The patient considered this a growth or mole. The lesion is described as rough or flaky and raised or bumpy. The back of the hand is involved. Fitzpatrick I; lay reviewers estimated Monk Skin Tone 2 (US pool) or 1 (India pool). Female subject, age 30–39. The lesion is associated with pain, enlargement and bothersome appearance. Associated systemic symptoms include joint pain. The condition has been present for more than one year. This image was taken at an angle: 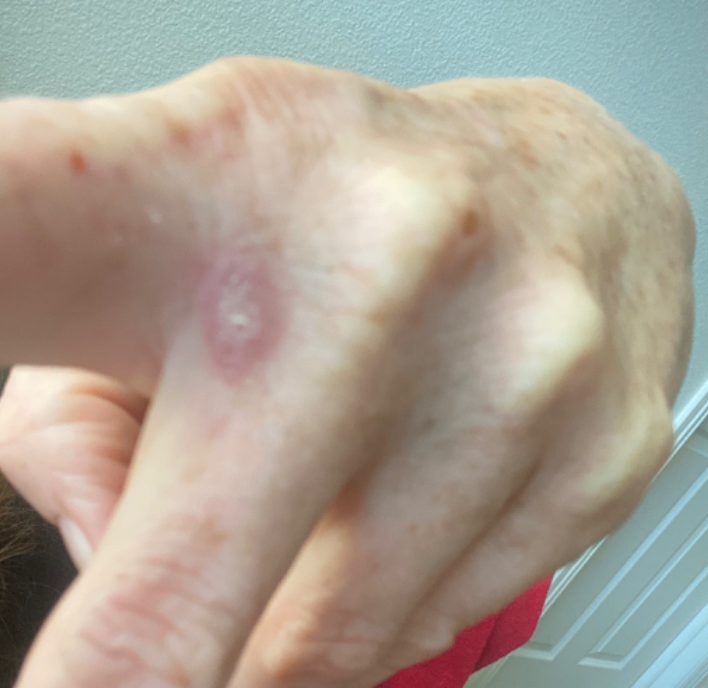  assessment: indeterminate from the photograph